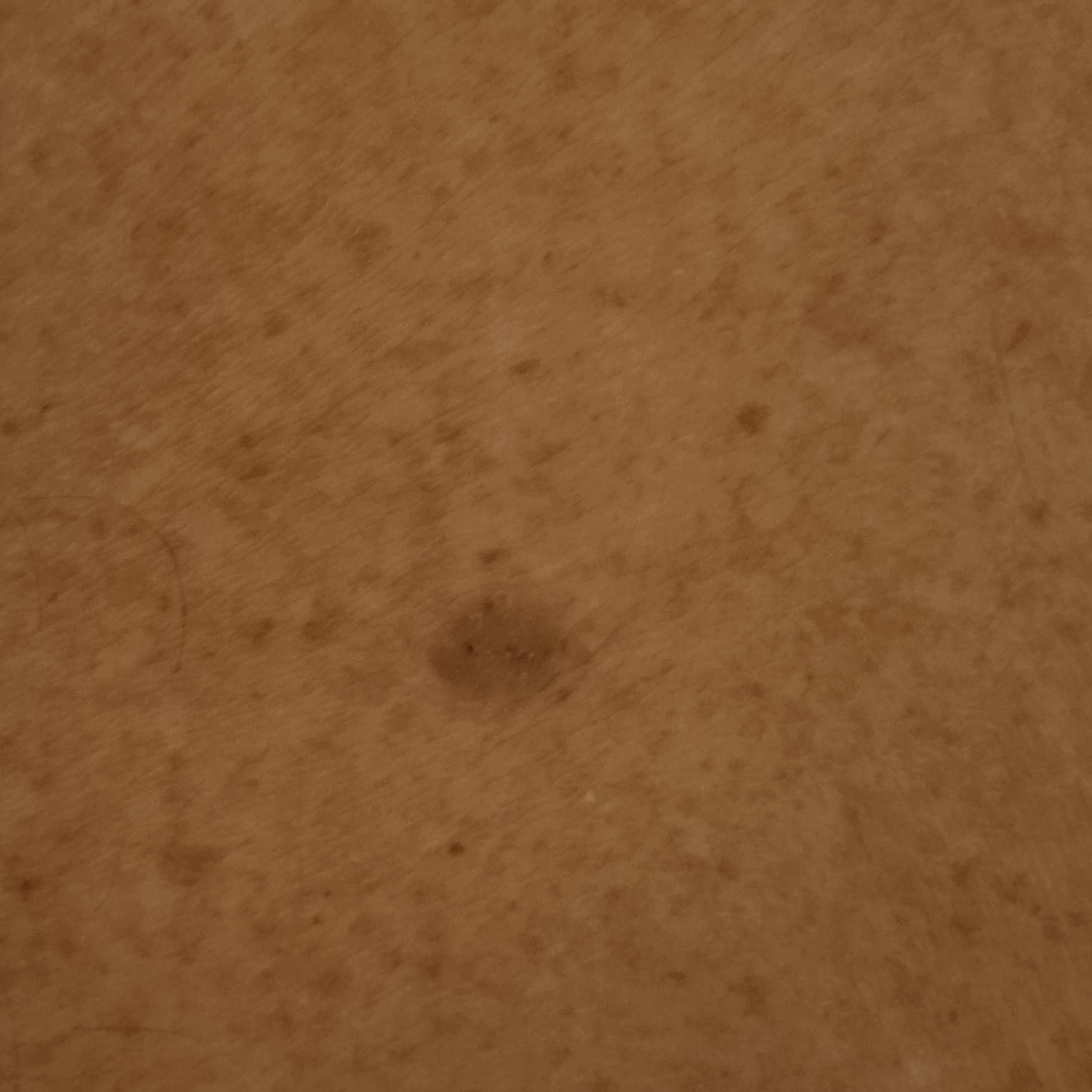diagnosis = seborrheic keratosis (dermatologist consensus).